The photograph was taken at an angle; the lesion involves the leg; female contributor, age 50–59: 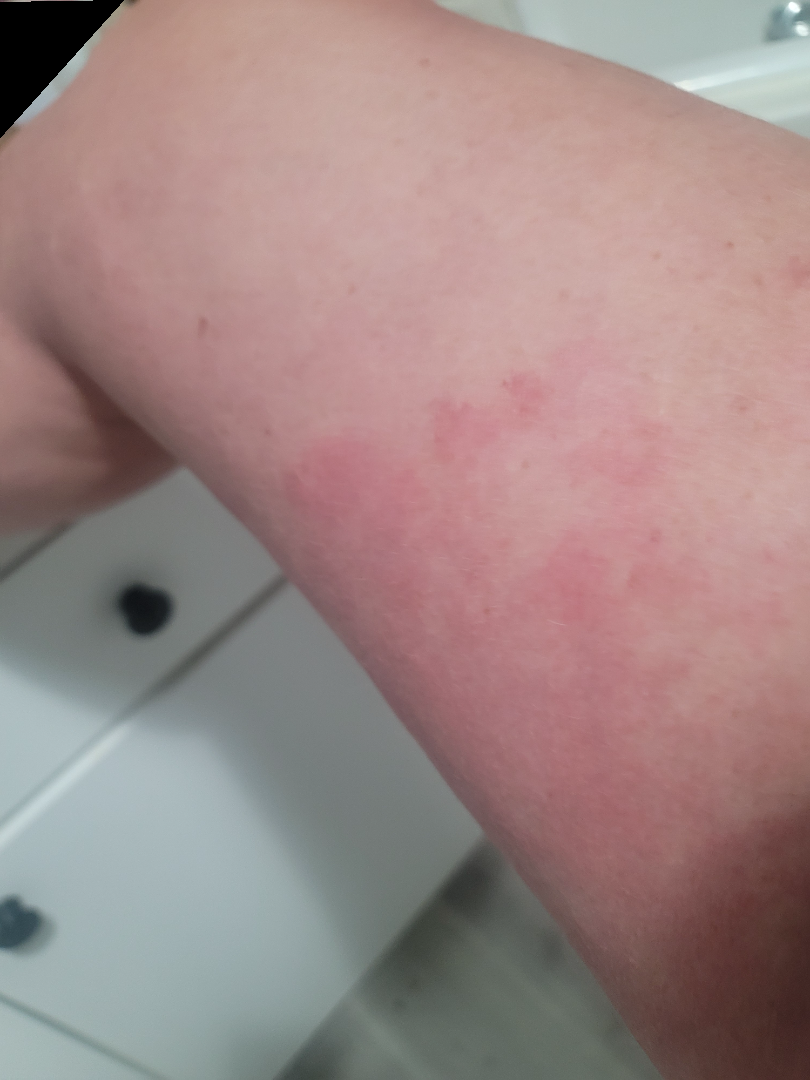| key | value |
|---|---|
| assessment | Hypersensitivity (0.33); Allergic Contact Dermatitis (0.33); Erythema migrans (0.33) |